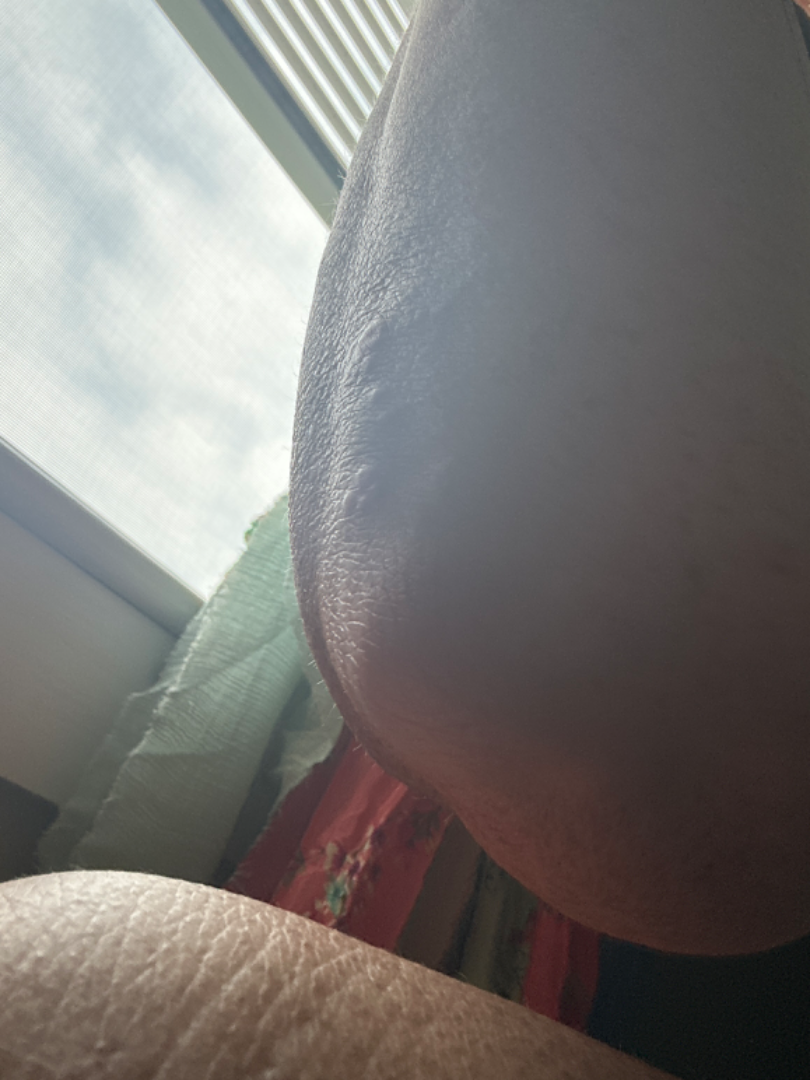texture — raised or bumpy | systemic symptoms — none reported | body site — arm | framing — at an angle | history — more than one year | diagnostic considerations — Granuloma annulare (possible); Insect Bite (possible); Allergic Contact Dermatitis (possible).